A female subject 68 years old; history notes prior skin cancer (patient or family) and prior malignancy (patient or family).
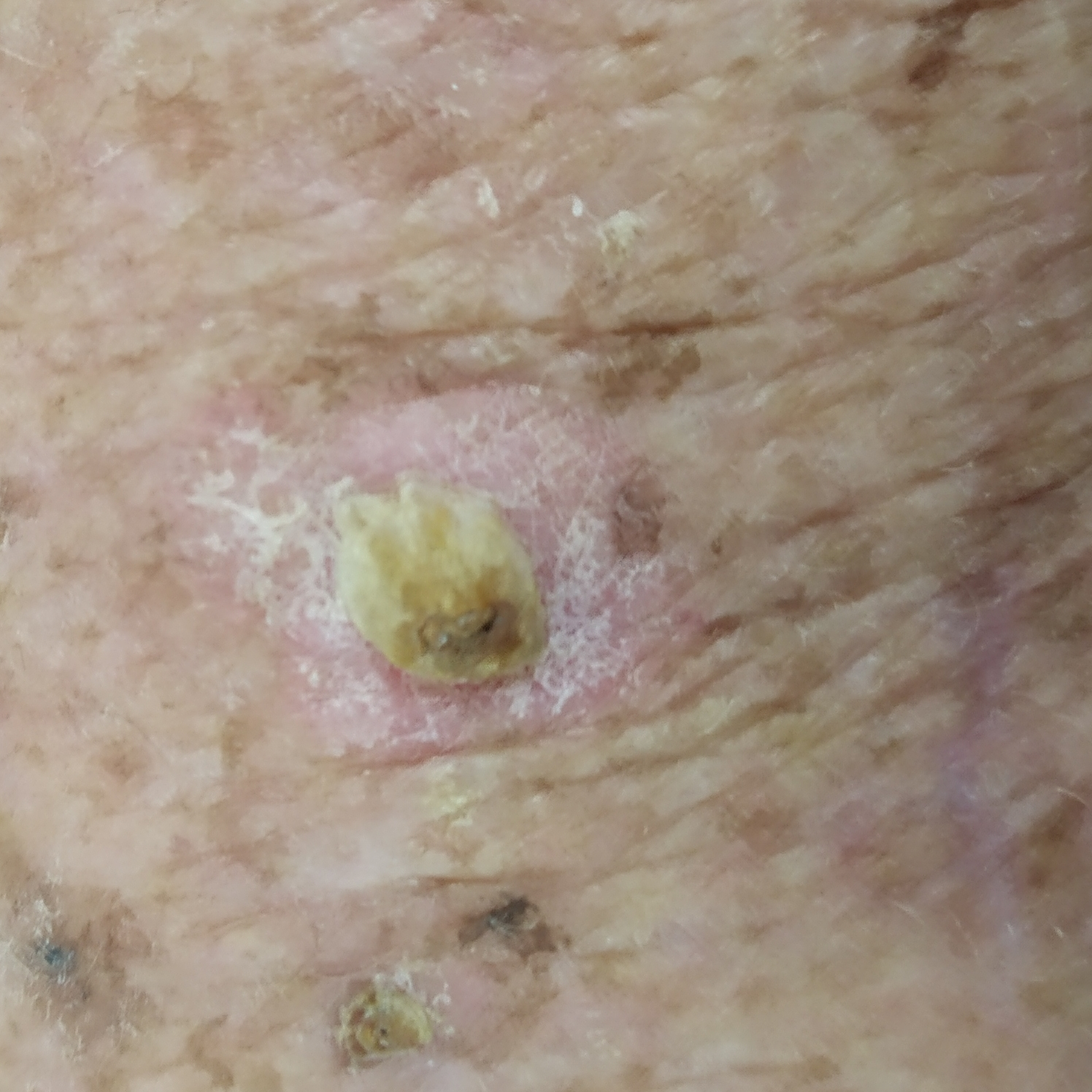diagnostic label = actinic keratosis (biopsy-proven)